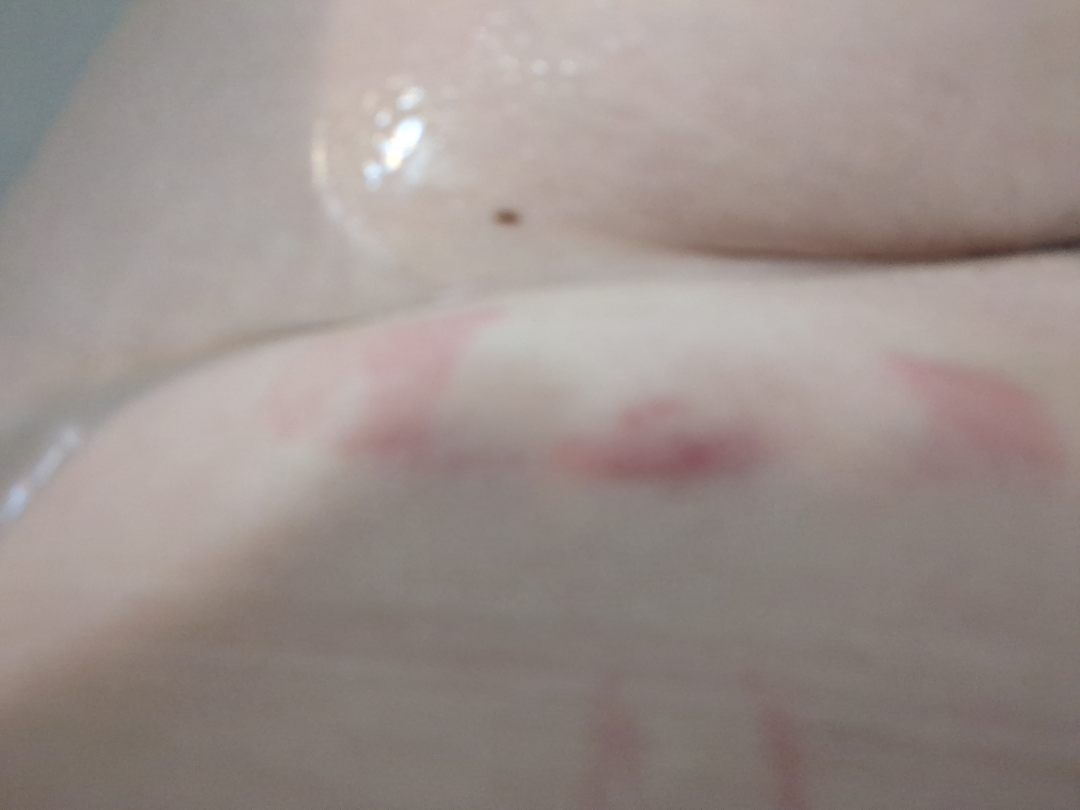| feature | finding |
|---|---|
| differential diagnosis | Allergic Contact Dermatitis (most likely) |